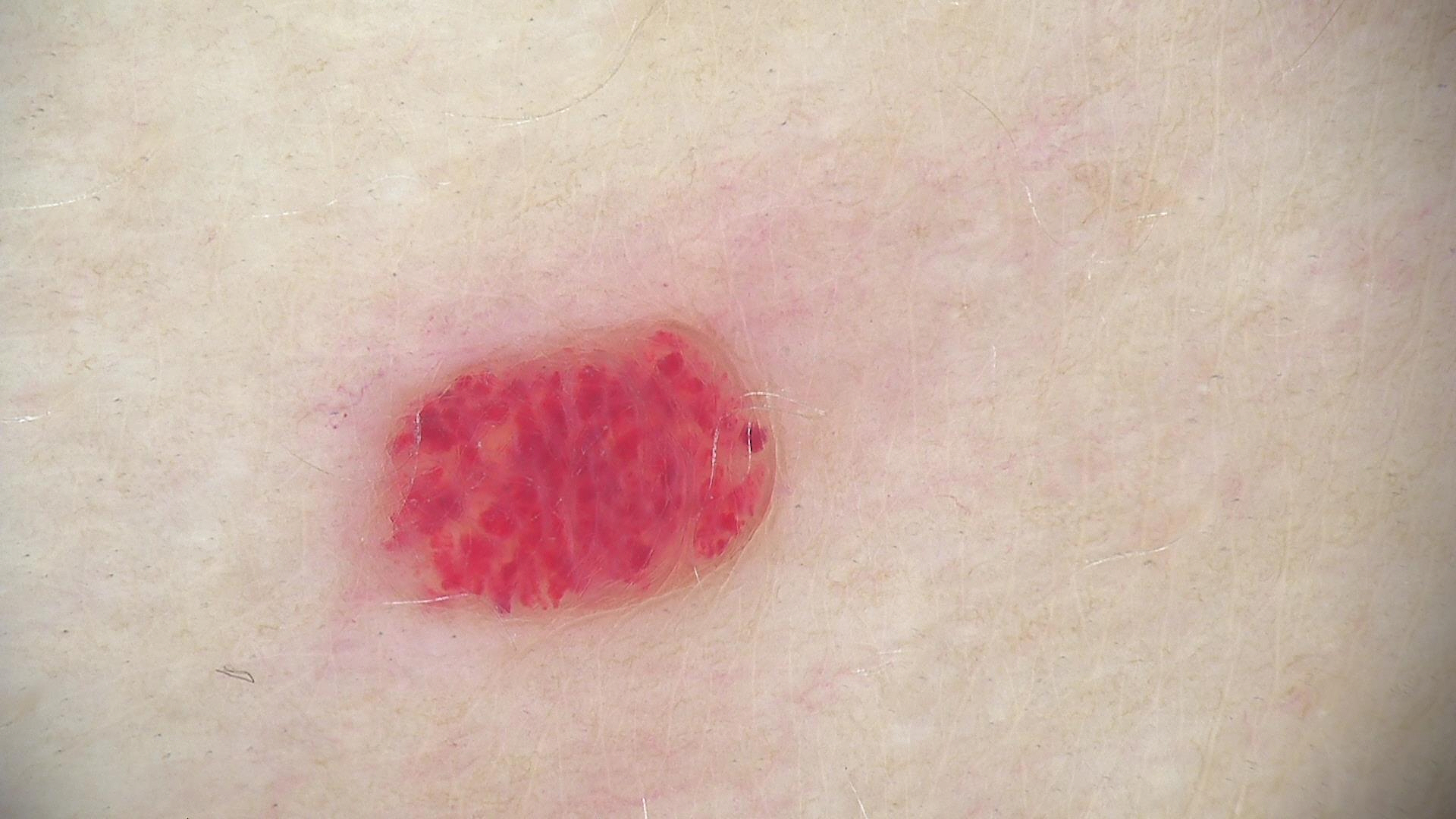subtype=vascular; diagnosis=hemangioma (expert consensus).